Located on the palm · reported lesion symptoms include pain, enlargement, bothersome appearance and itching · the lesion is described as raised or bumpy and rough or flaky · the patient is 40–49, female · reported duration is one to four weeks · the patient notes associated mouth sores · an image taken at an angle · the patient described the issue as a rash · skin tone: FST III; human graders estimated Monk skin tone scale 4 (US pool) or 3 (India pool) — 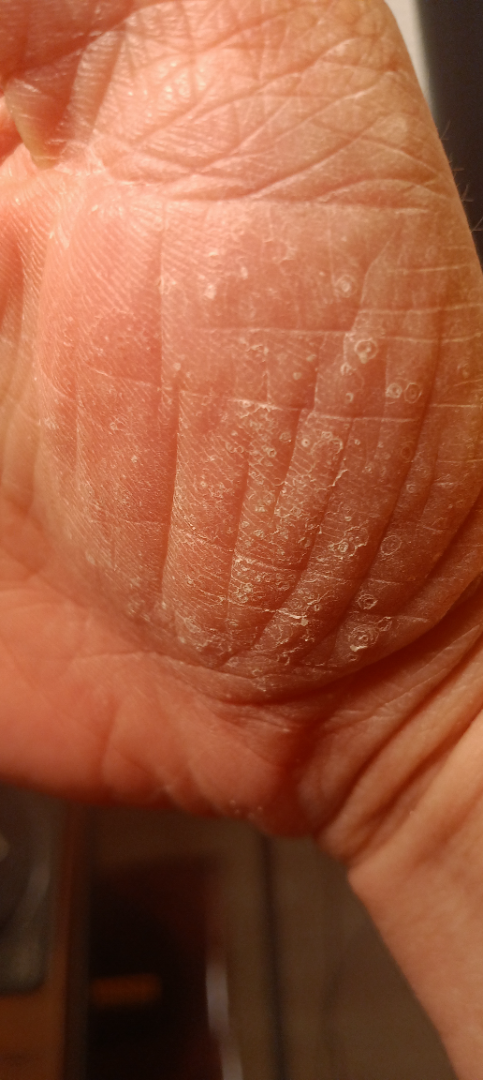On remote dermatologist review, Eczema and Psoriasis were each considered, in no particular order.